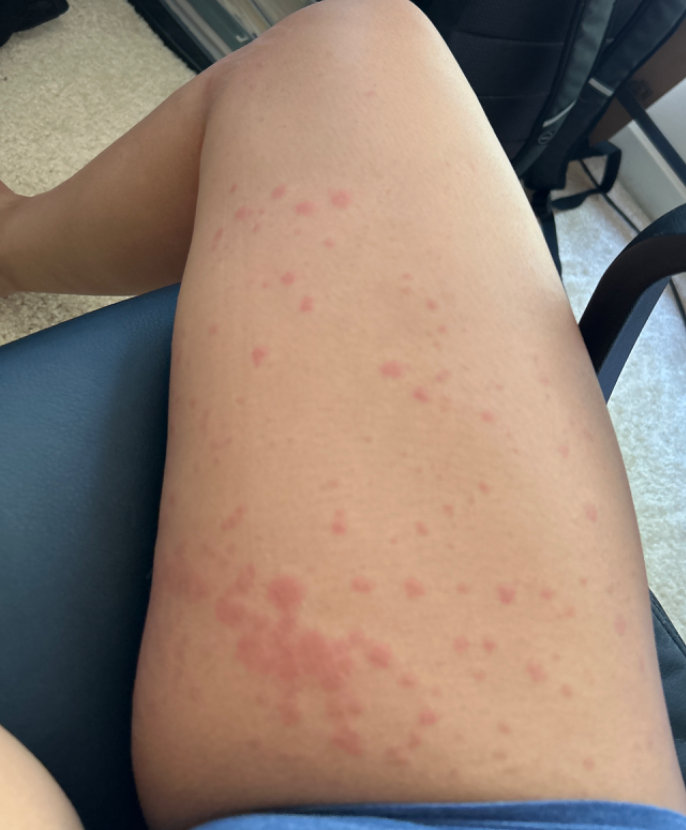site: sole of the foot, arm, leg, top or side of the foot, back of the hand and palm
patient: female, age 18–29
view: at a distance
dermatologist impression: the favored diagnosis is Urticaria; possibly Erythema multiforme; also consider Allergic Contact Dermatitis